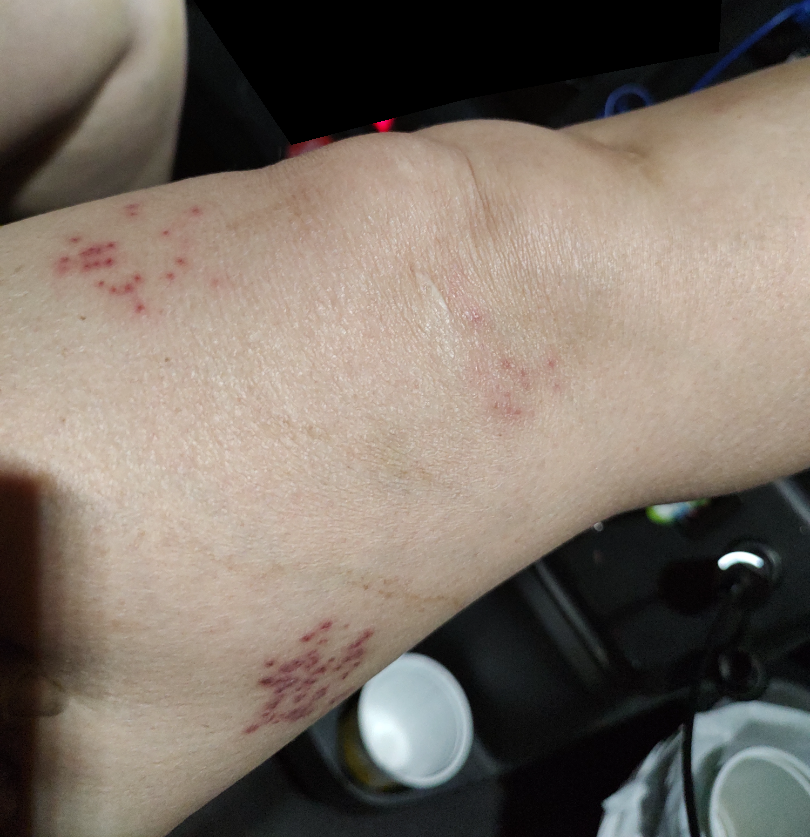The patient described the issue as a rash. Symptoms reported: bothersome appearance. The subject is a female aged 50–59. The leg is involved. The photo was captured at a distance. The leading consideration is Herpes Zoster; an alternative is Impetigo; the differential also includes Herpes Simplex.